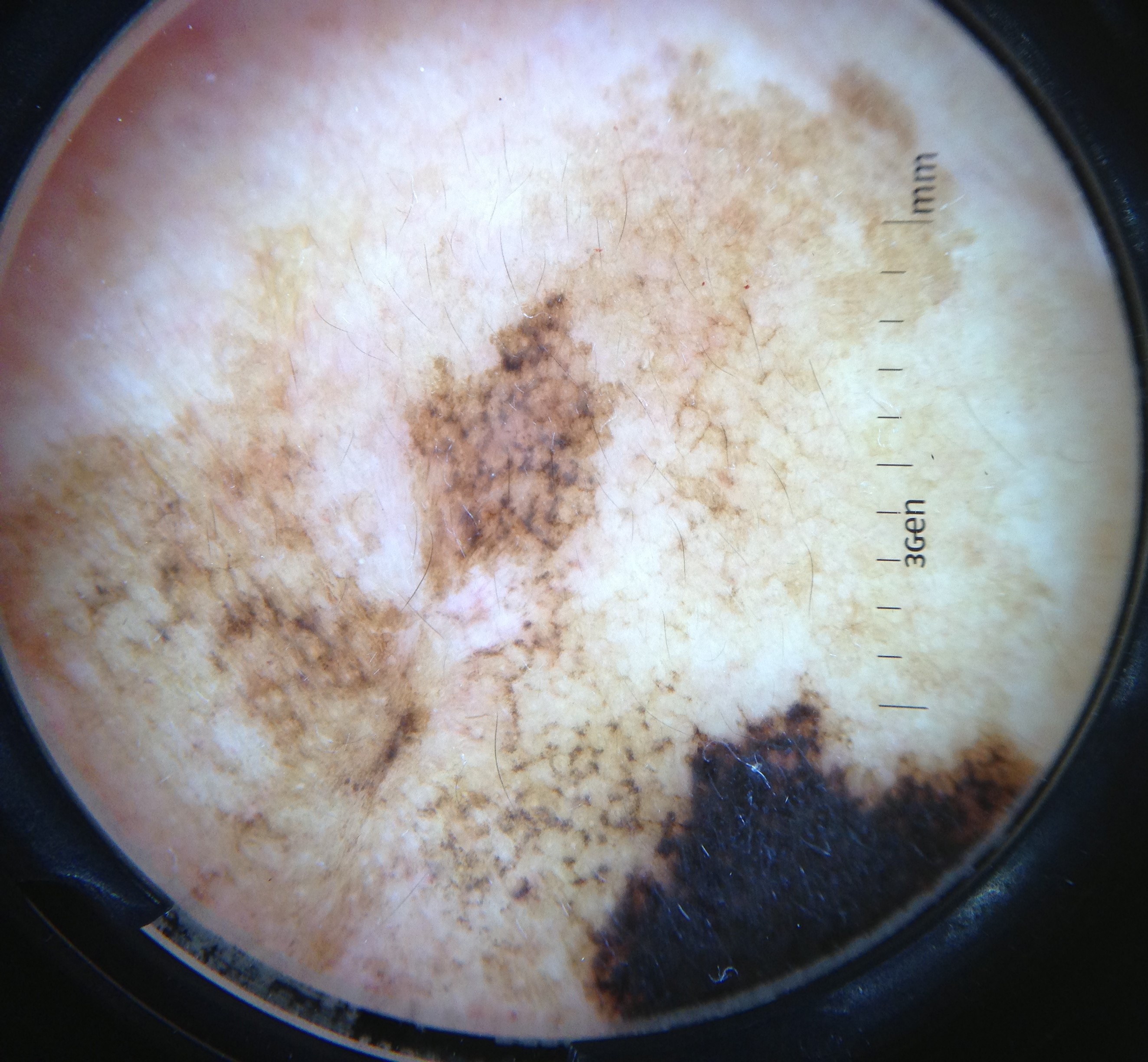Conclusion:
Confirmed on histopathology as a lentigo maligna.